A dermoscopic close-up of a skin lesion · a female patient aged approximately 40.
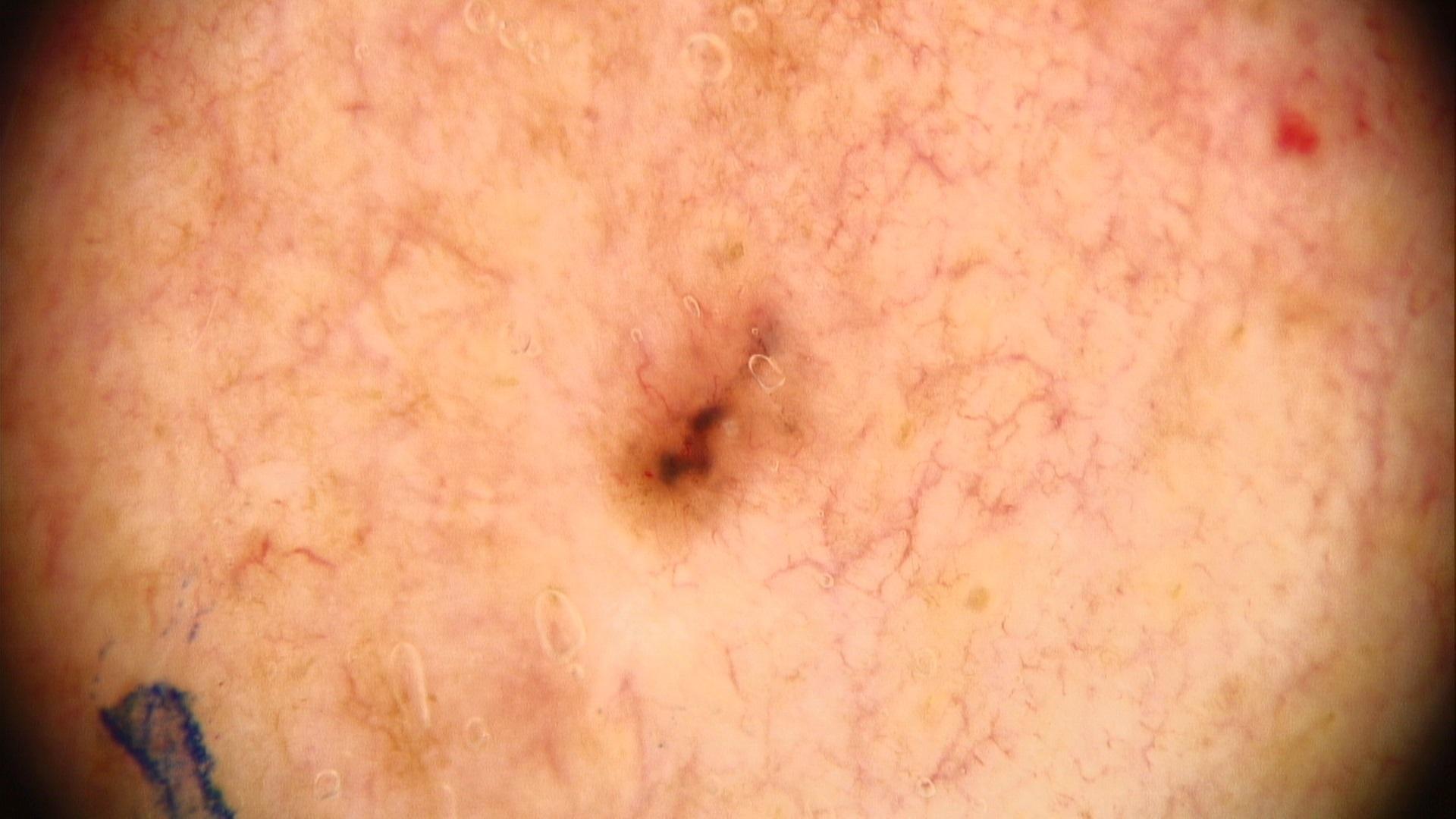Case:
– pathology · Basal cell carcinoma (biopsy-proven)